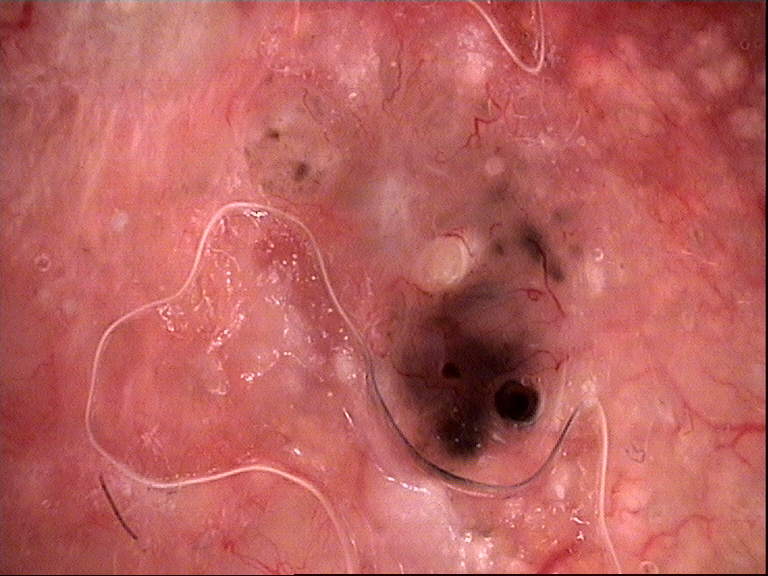{"image": "dermatoscopy", "diagnosis": {"name": "basal cell carcinoma", "code": "bcc", "malignancy": "malignant", "super_class": "non-melanocytic", "confirmation": "histopathology"}}